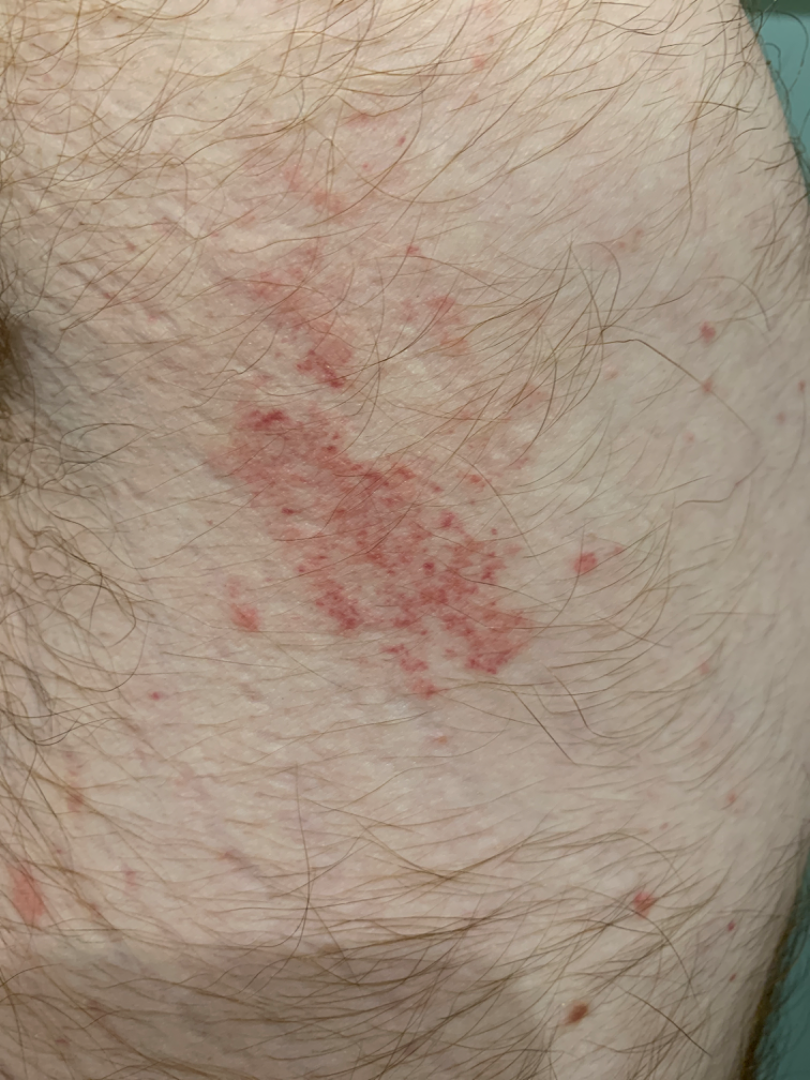On remote review of the image: Eczema and Allergic Contact Dermatitis were considered with similar weight.